This is a dermoscopic photograph of a skin lesion:
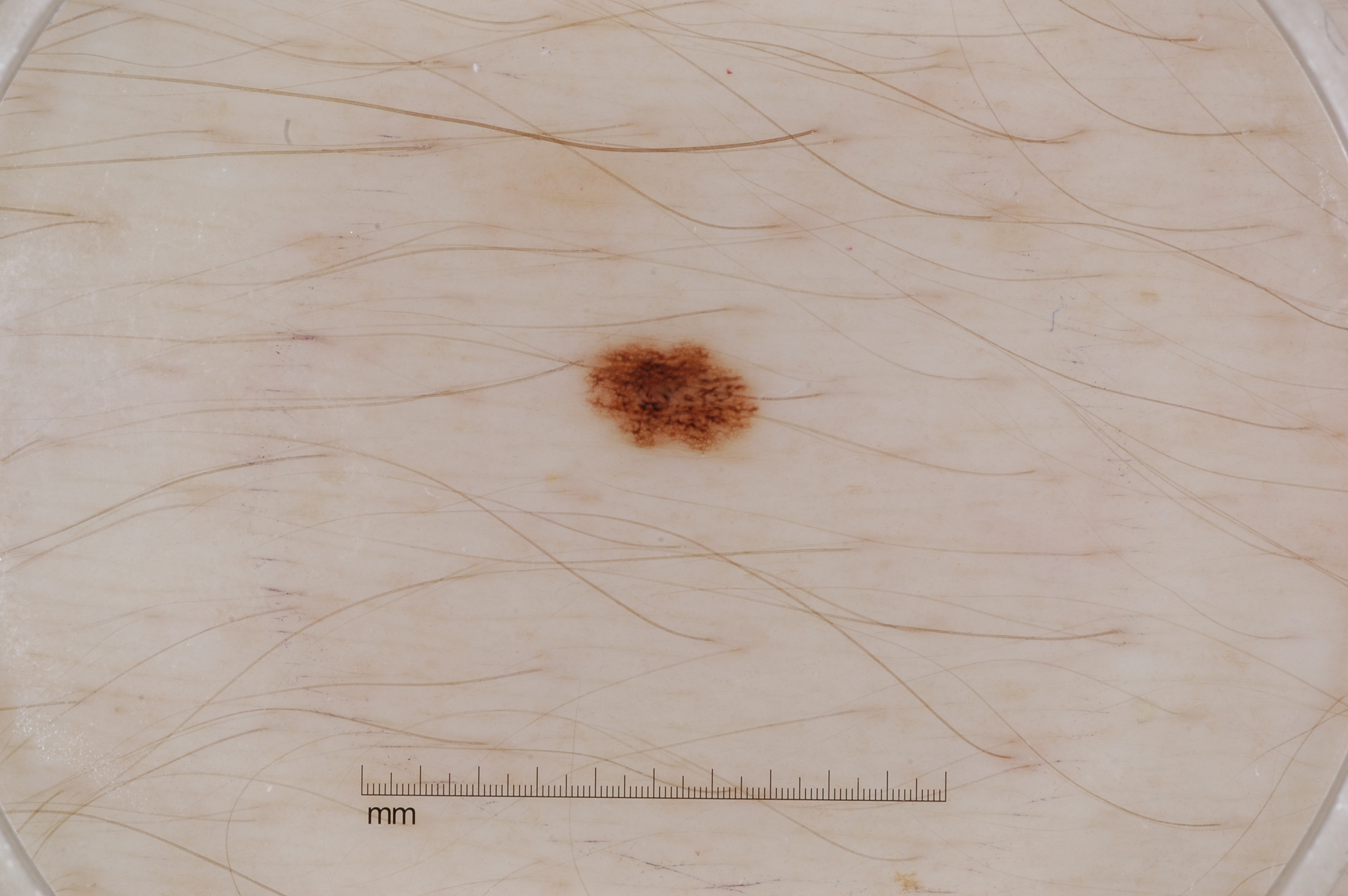<record>
<dermoscopic_features>
  <present>pigment network</present>
  <absent>streaks, milia-like cysts, negative network</absent>
</dermoscopic_features>
<lesion_location>
  <bbox_xyxy>590, 336, 758, 455</bbox_xyxy>
</lesion_location>
<diagnosis>
  <name>melanocytic nevus</name>
  <malignancy>benign</malignancy>
  <lineage>melanocytic</lineage>
  <provenance>clinical</provenance>
</diagnosis>
</record>